This is a dermoscopic photograph of a skin lesion; a male patient, aged 48 to 52.
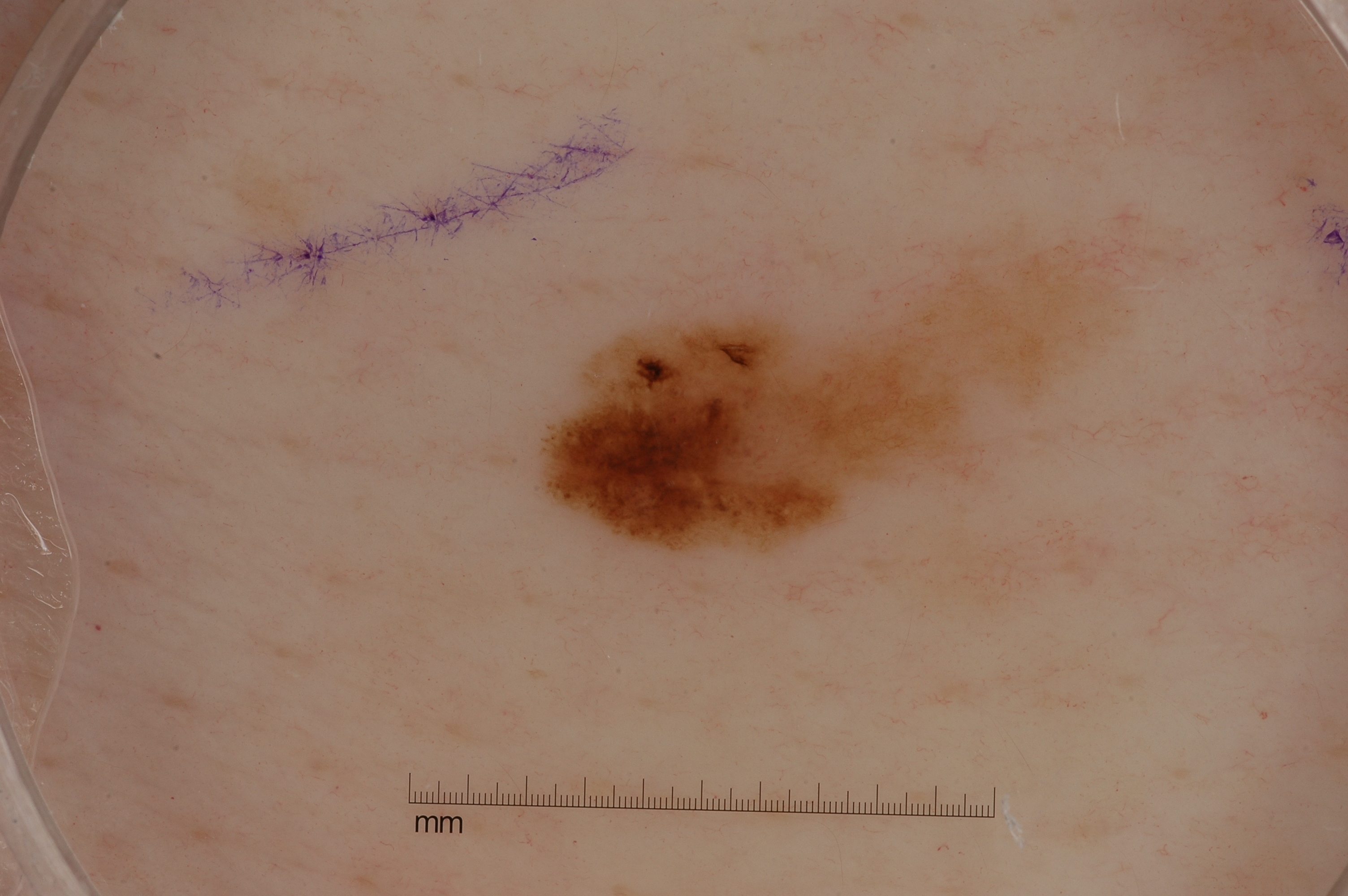In (x1, y1, x2, y2) order, the lesion is located at (548, 252, 1106, 553). Dermoscopic assessment notes pigment network; no streaks, milia-like cysts, or negative network. A small lesion occupying a minor part of the field. Confirmed on histopathology as a melanoma.